A skin lesion imaged with a dermatoscope:
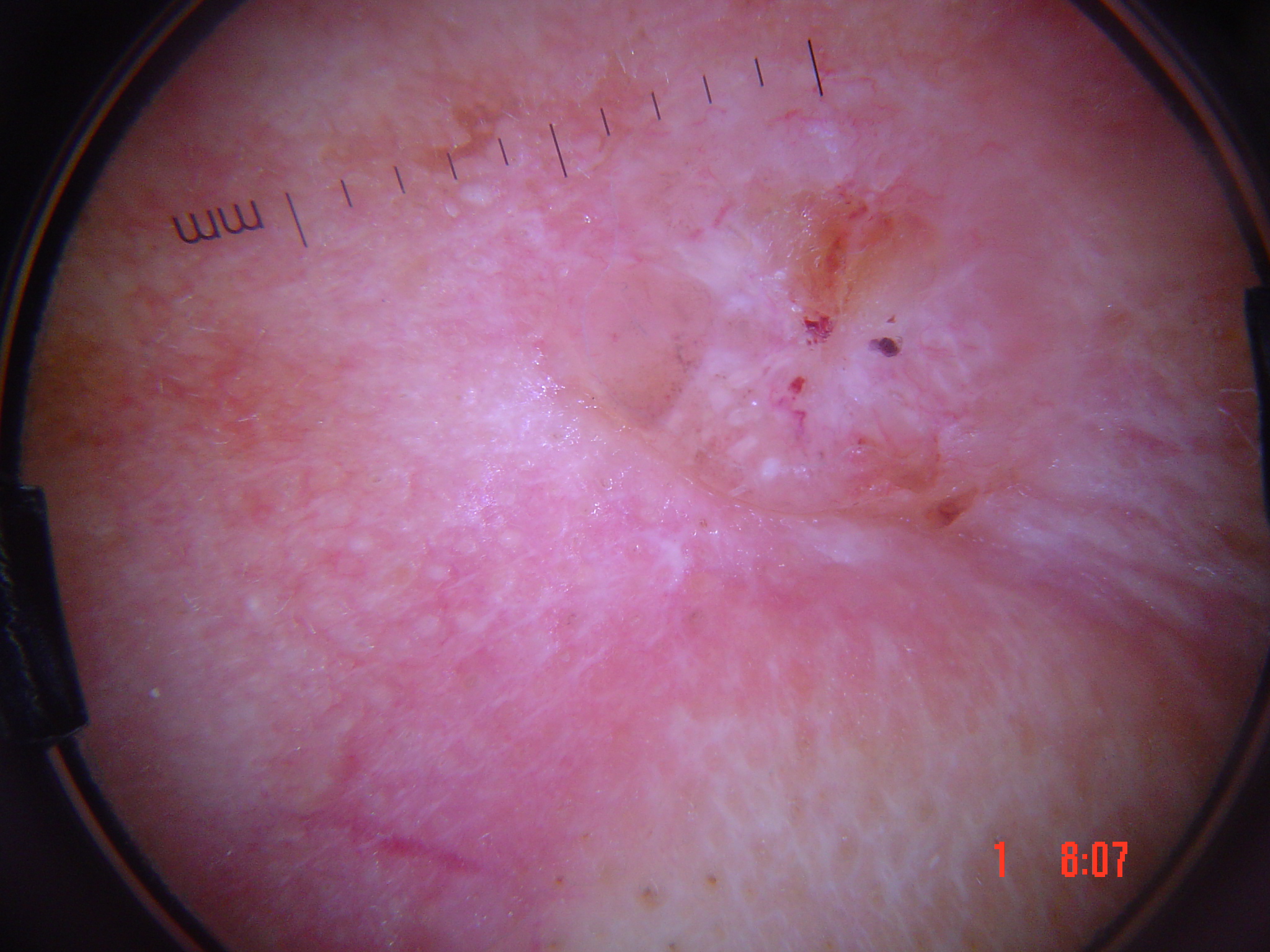The biopsy diagnosis was a basal cell carcinoma.